Dermoscopy of a skin lesion: 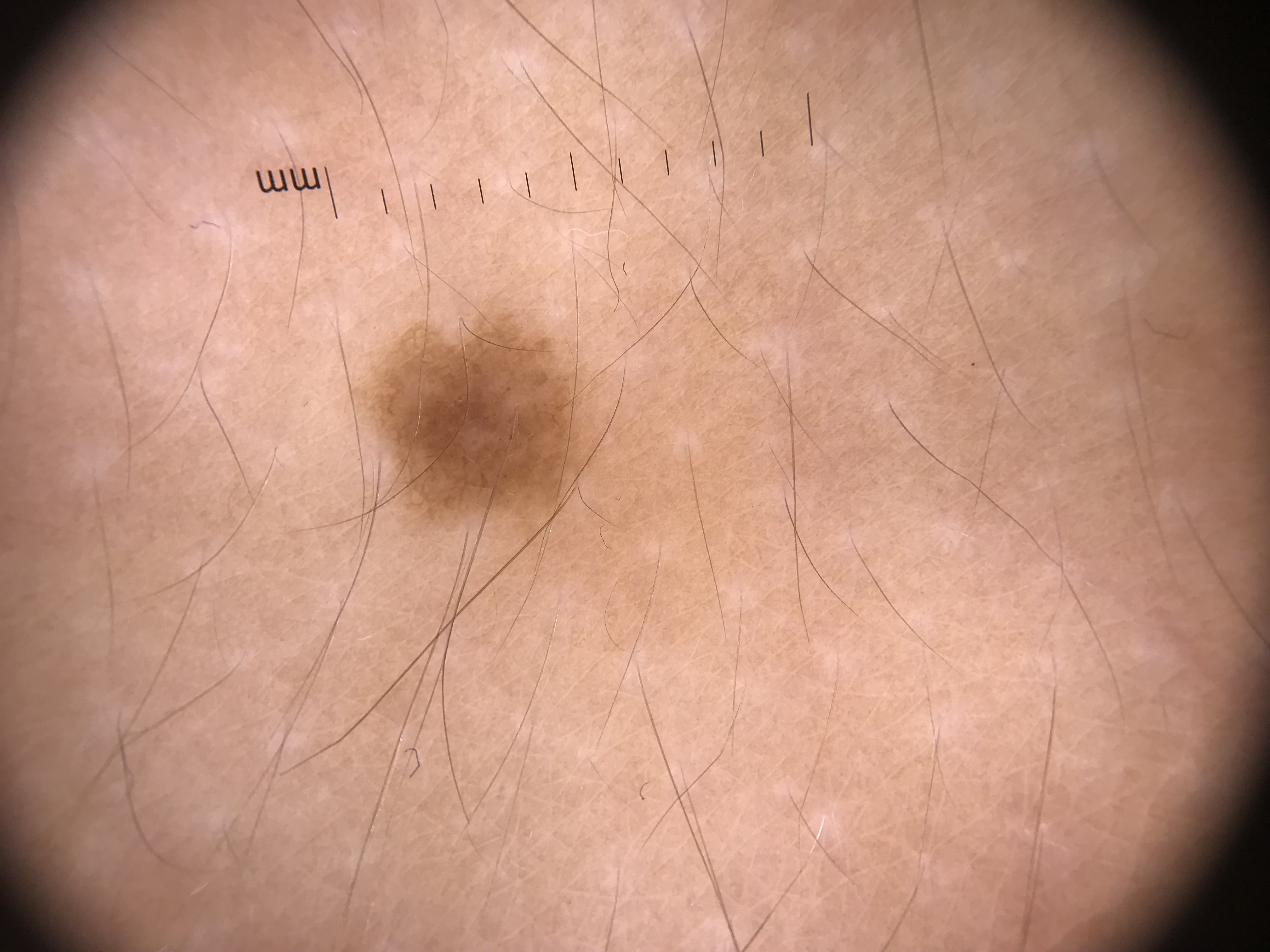Labeled as a banal lesion — a junctional nevus.